Dermoscopy of a skin lesion.
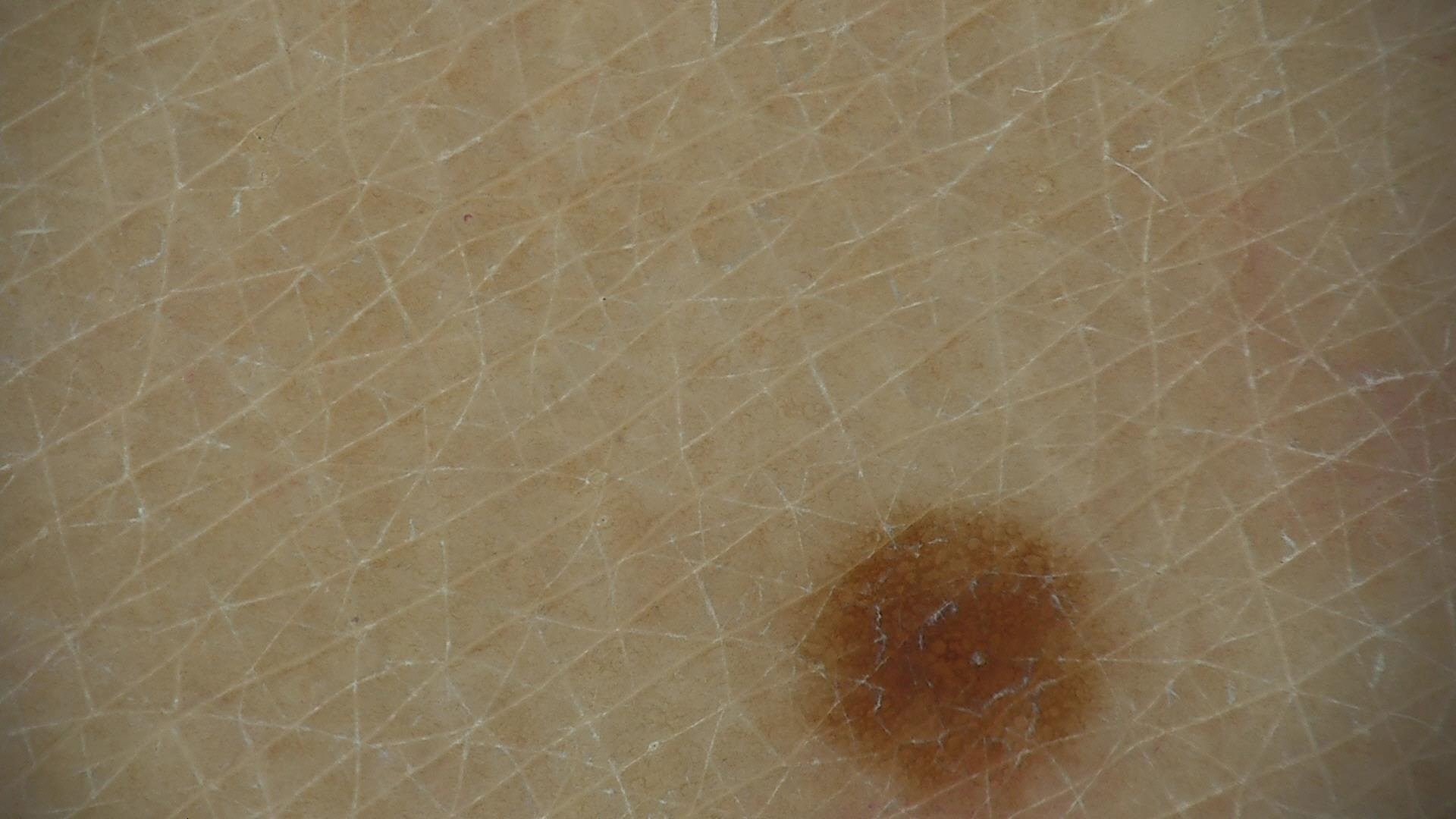Impression:
The diagnosis was a banal lesion — a junctional nevus.